The patient is Fitzpatrick phototype II.
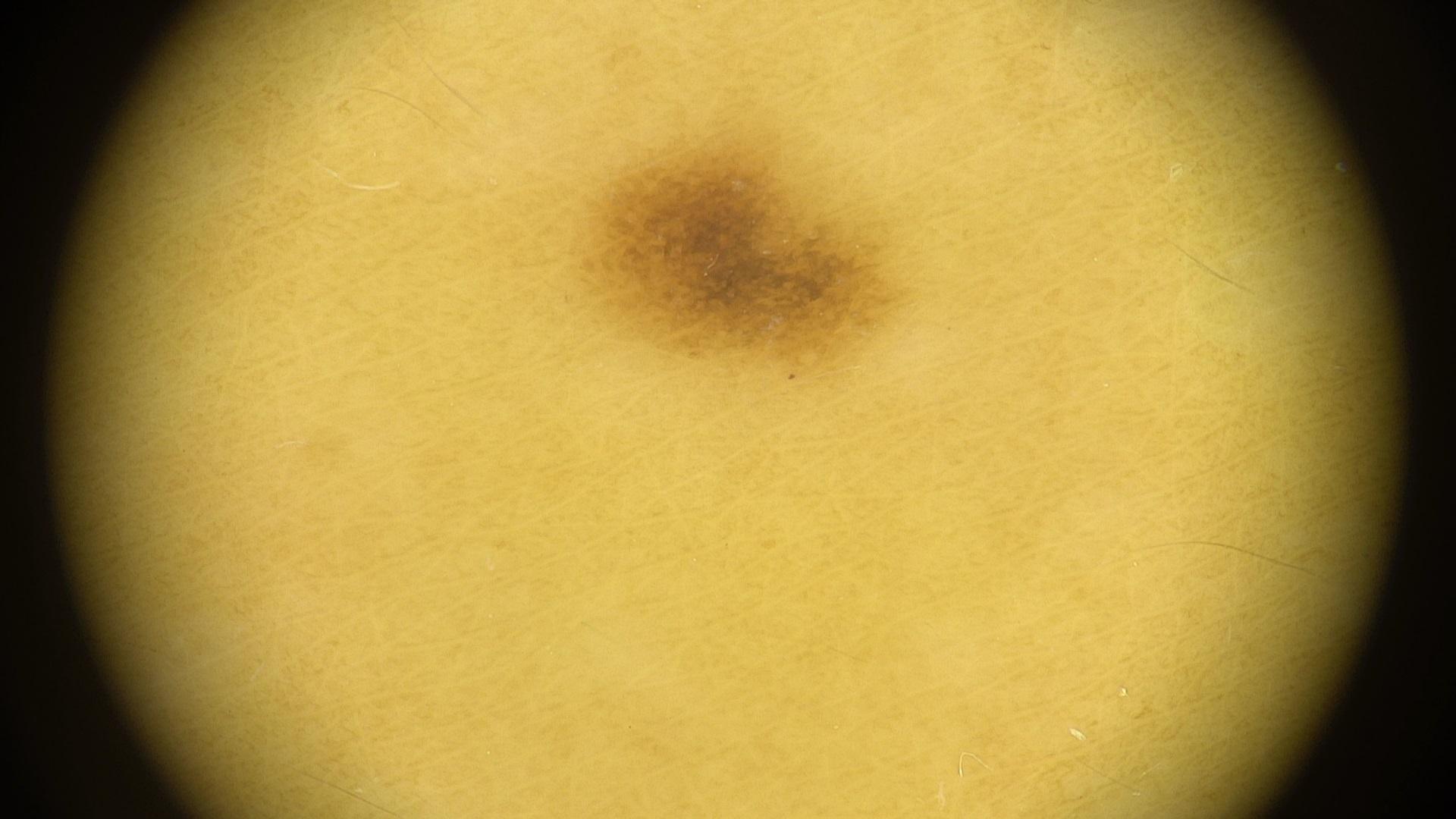Conclusion: The clinical assessment was a nevus.